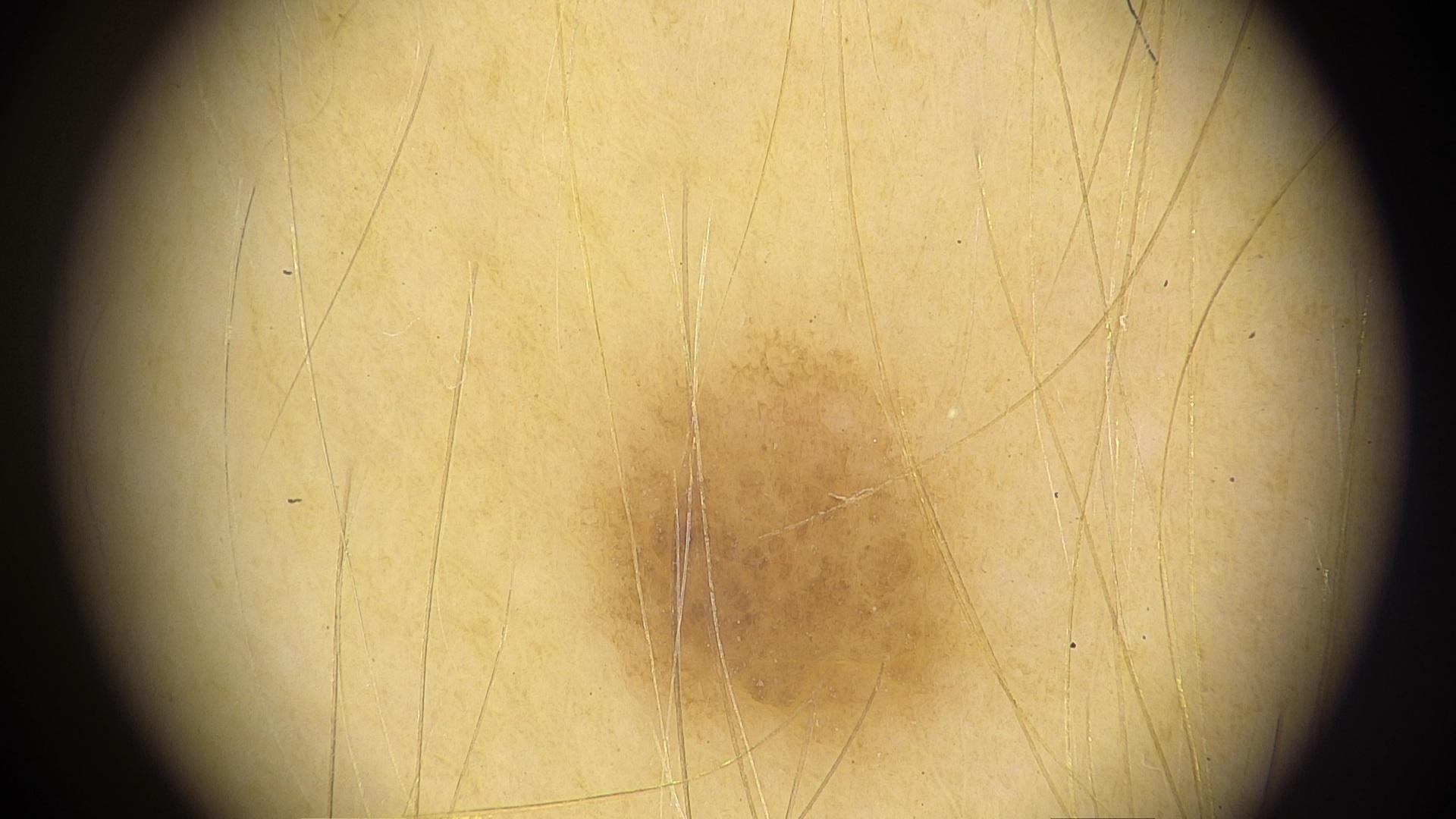Case:
– subject · female, roughly 50 years of age
– imaging · dermatoscopic image
– melanoma history · a previous melanoma but no melanoma in first-degree relatives
– FST · II
– location · the anterior trunk
– diagnosis · Nevus (clinical impression)